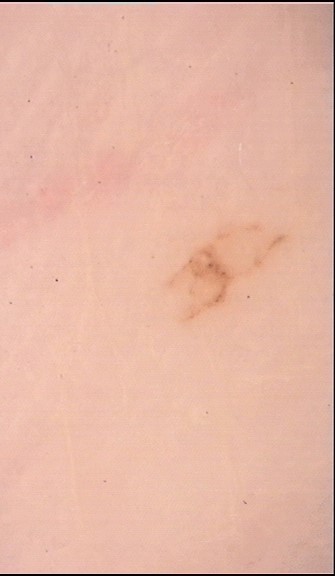Findings:
* image type — dermoscopy
* diagnostic label — acral junctional nevus (expert consensus)